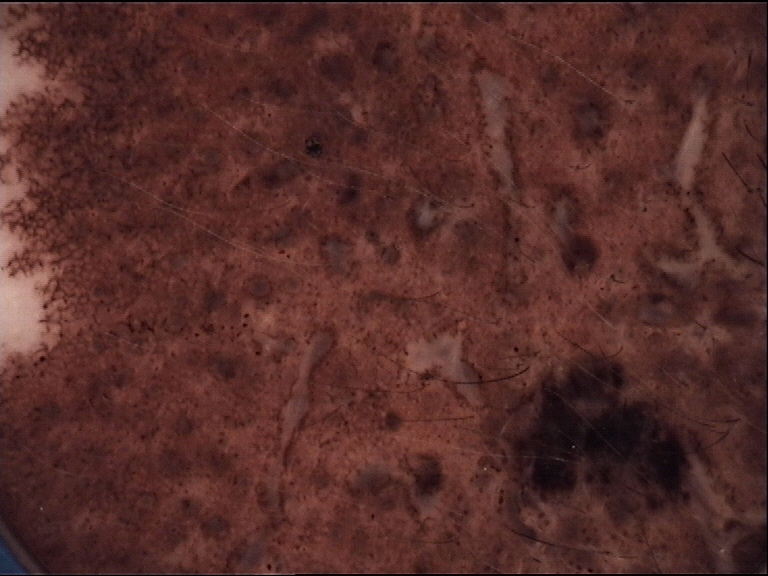Findings:
A dermoscopic close-up of a skin lesion.
Impression:
The diagnosis was a banal lesion — a congenital compound nevus.